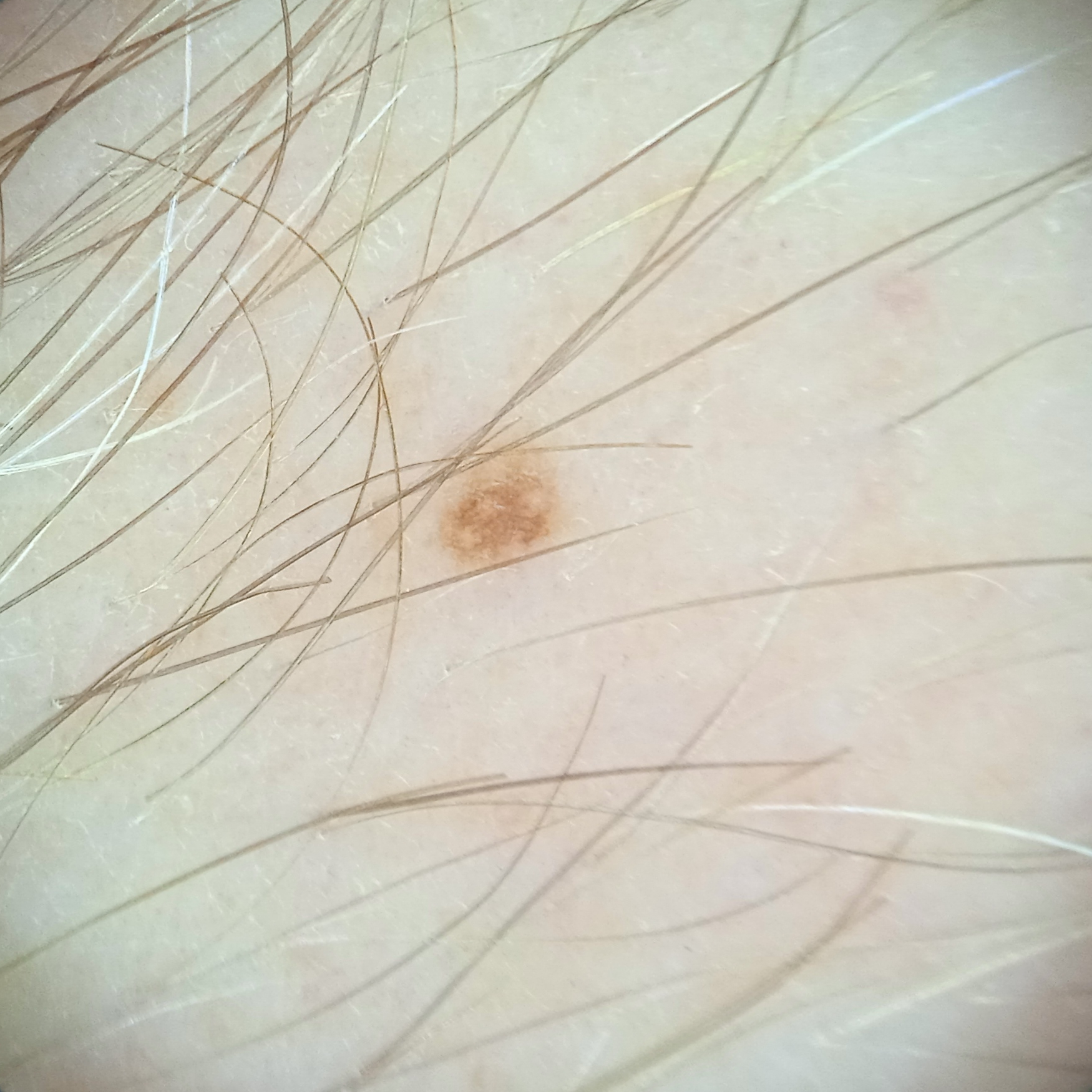Acquired for a research image collection, with no referral diagnosis. By self-report, no immunosuppression and no personal history of skin cancer. The patient says their skin reddens with sun exposure. A male patient 60 years of age. Dermoscopy of a skin lesion. The lesion is on an arm. Measuring roughly 1.5 mm. The diagnostic impression was a melanocytic nevus.